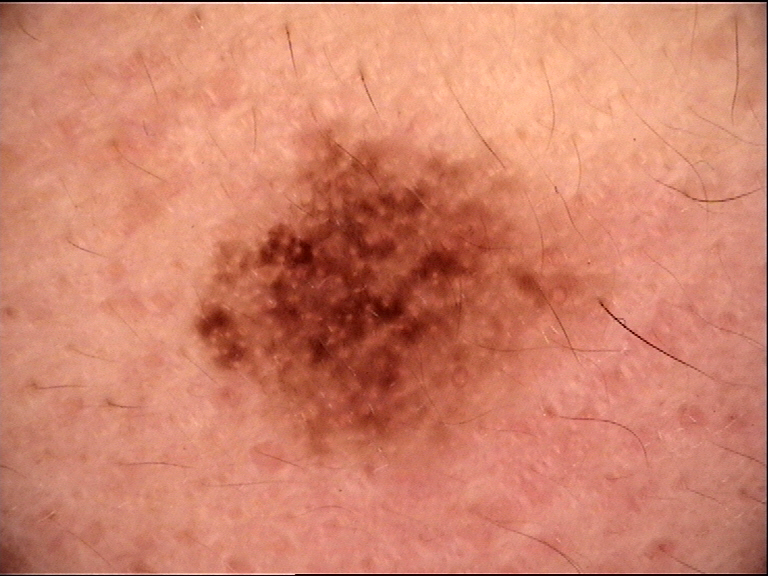category = banal, compound | assessment = Miescher nevus (expert consensus).